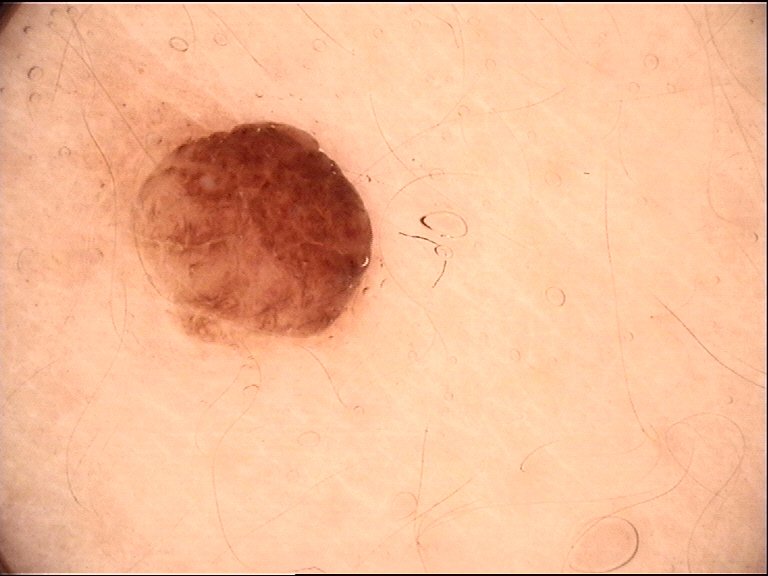Findings:
- imaging — dermatoscopy
- class — dermal nevus (expert consensus)